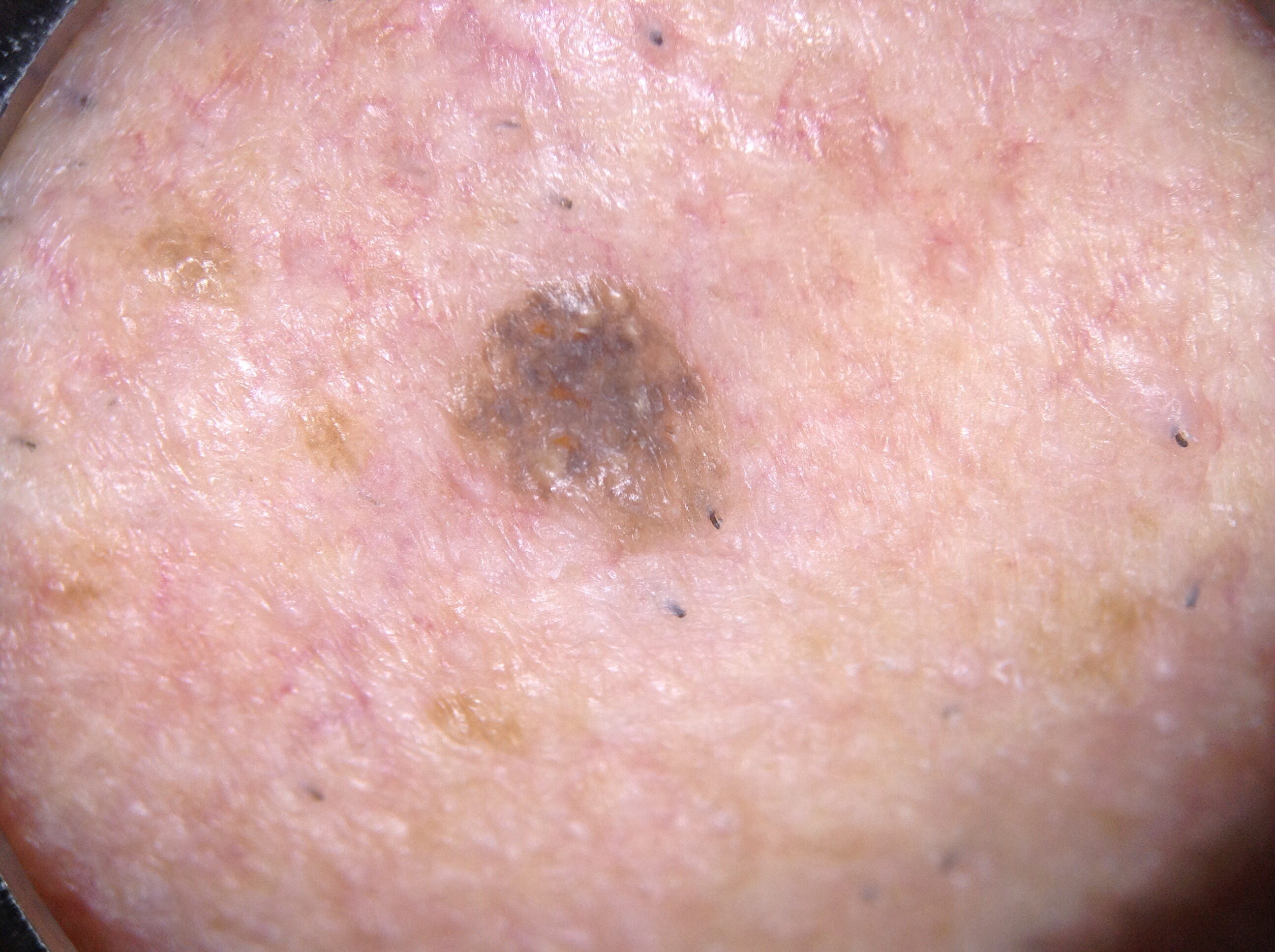image=dermoscopy of a skin lesion | absent dermoscopic findings=milia-like cysts, streaks, pigment network, and negative network | lesion extent=small | lesion location=<box>427, 255, 753, 566</box> | impression=a seborrheic keratosis, a benign lesion.